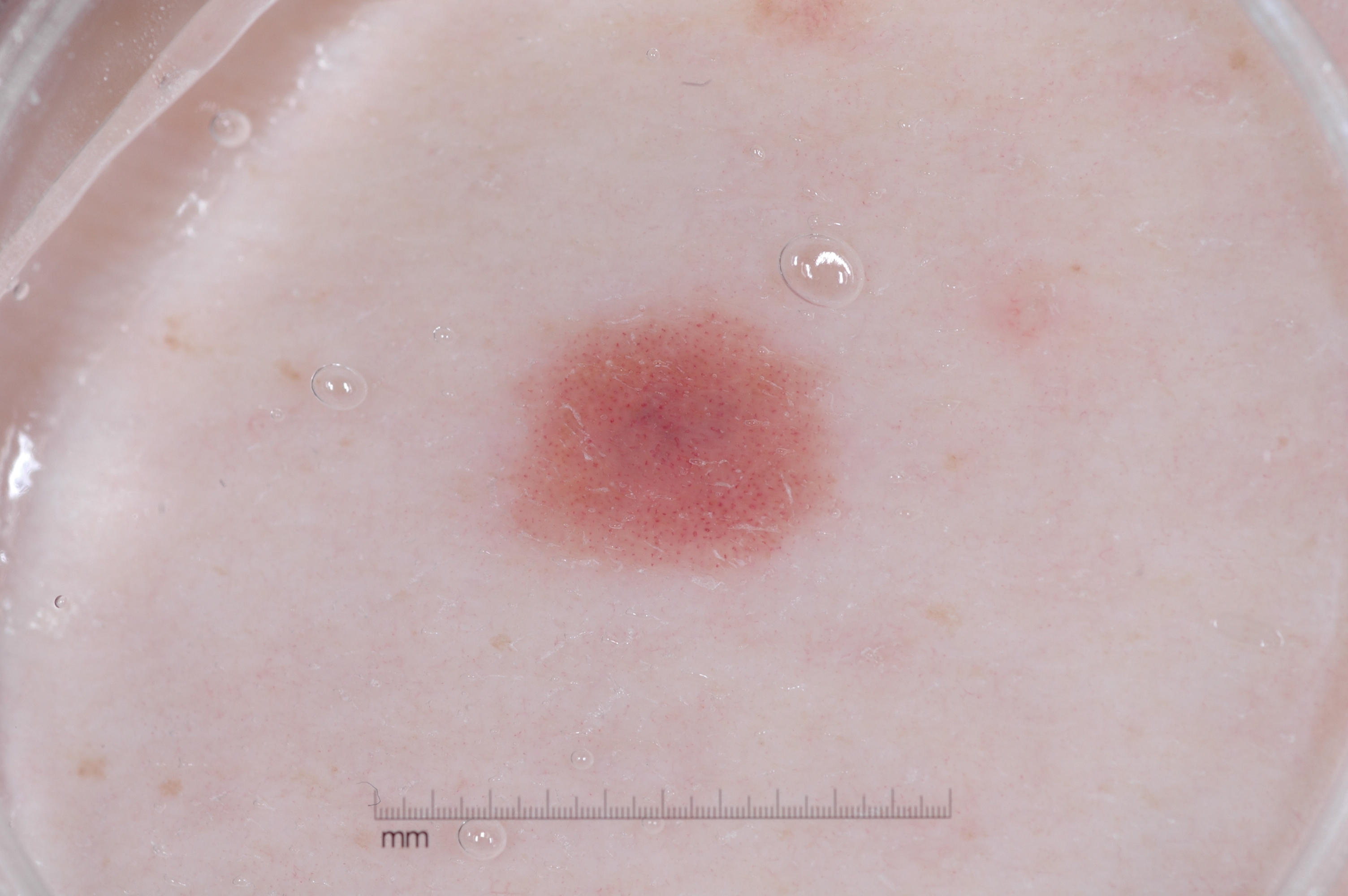Dermoscopy of a skin lesion. With coordinates (x1, y1, x2, y2), the lesion's extent is <bbox>495, 301, 832, 574</bbox>. Dermoscopic review identifies milia-like cysts; no negative network, pigment network, or streaks. A small lesion occupying a minor part of the field. Clinically diagnosed as a melanocytic nevus.